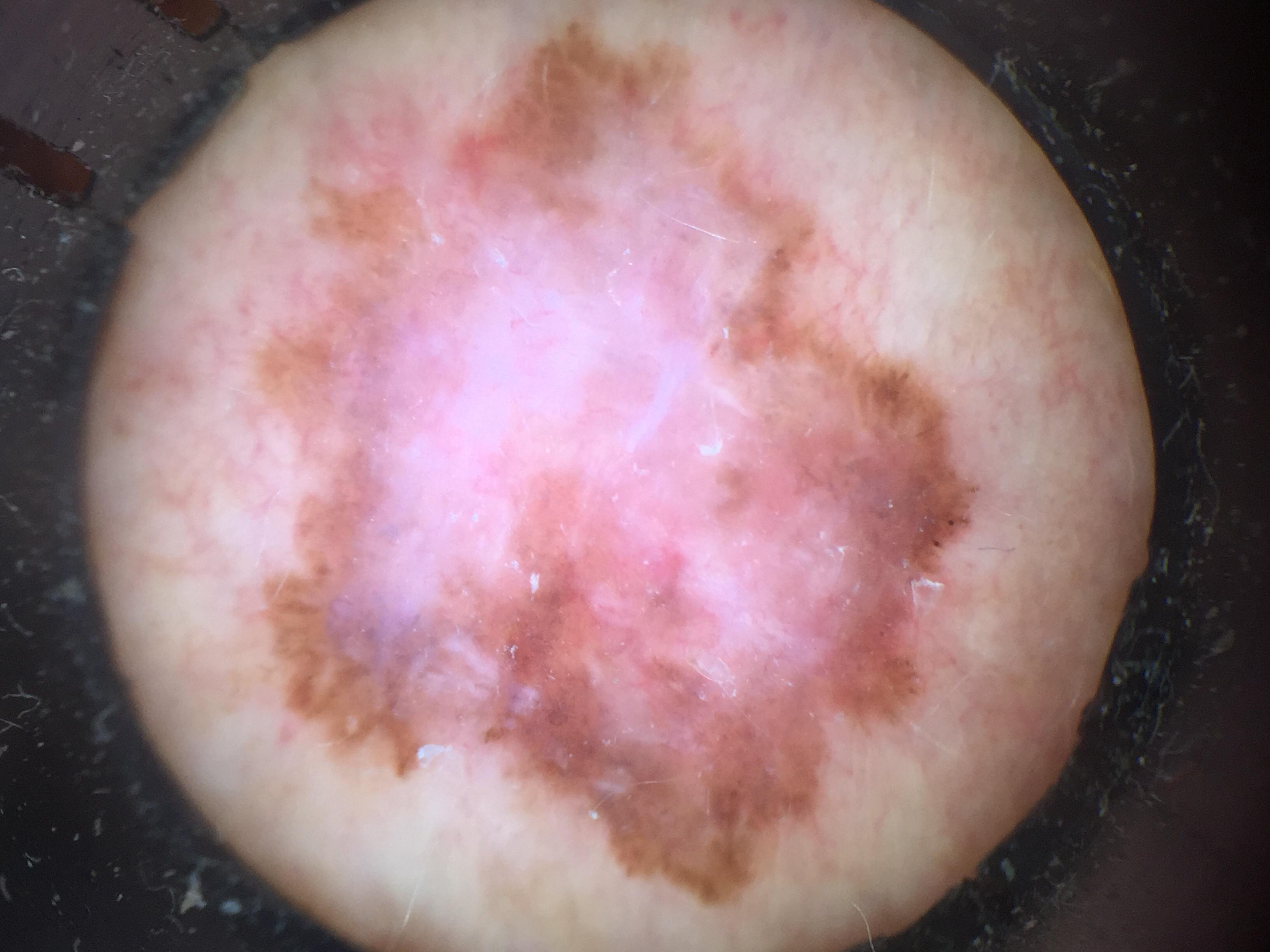Q: How was this image acquired?
A: contact-polarized dermoscopy
Q: Patient demographics?
A: female, about 75 years old
Q: What did the workup show?
A: Melanoma (biopsy-proven)